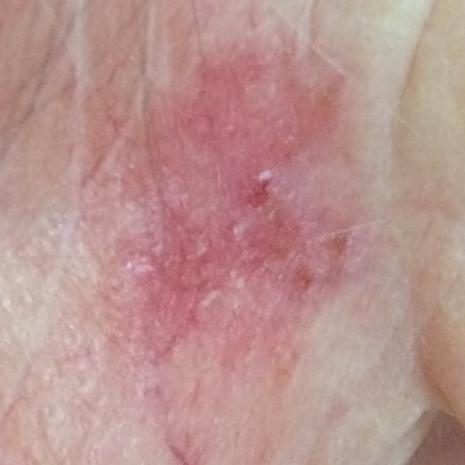The chart notes prior malignancy (patient or family). Skin type II. A clinical photograph showing a skin lesion. A female subject 77 years old. Located on an ear. Per patient report, the lesion has grown and is elevated. Histopathologically confirmed as a squamous cell carcinoma.